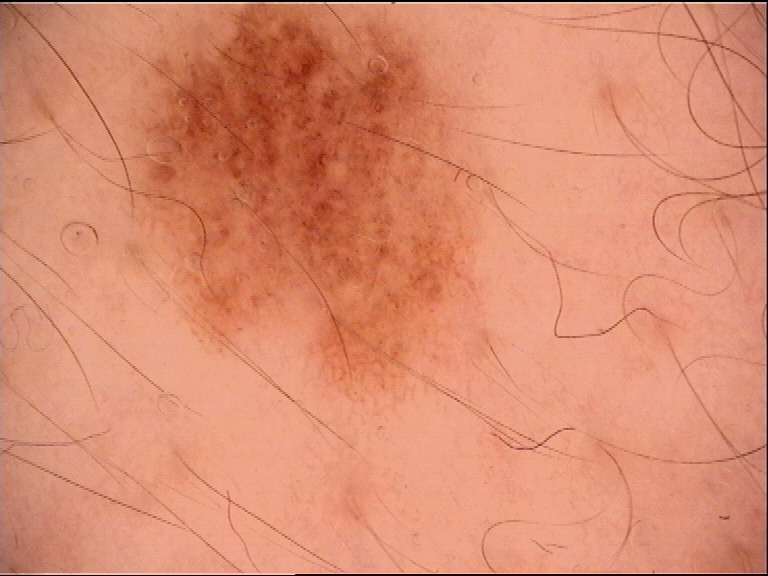Labeled as a dysplastic junctional nevus.